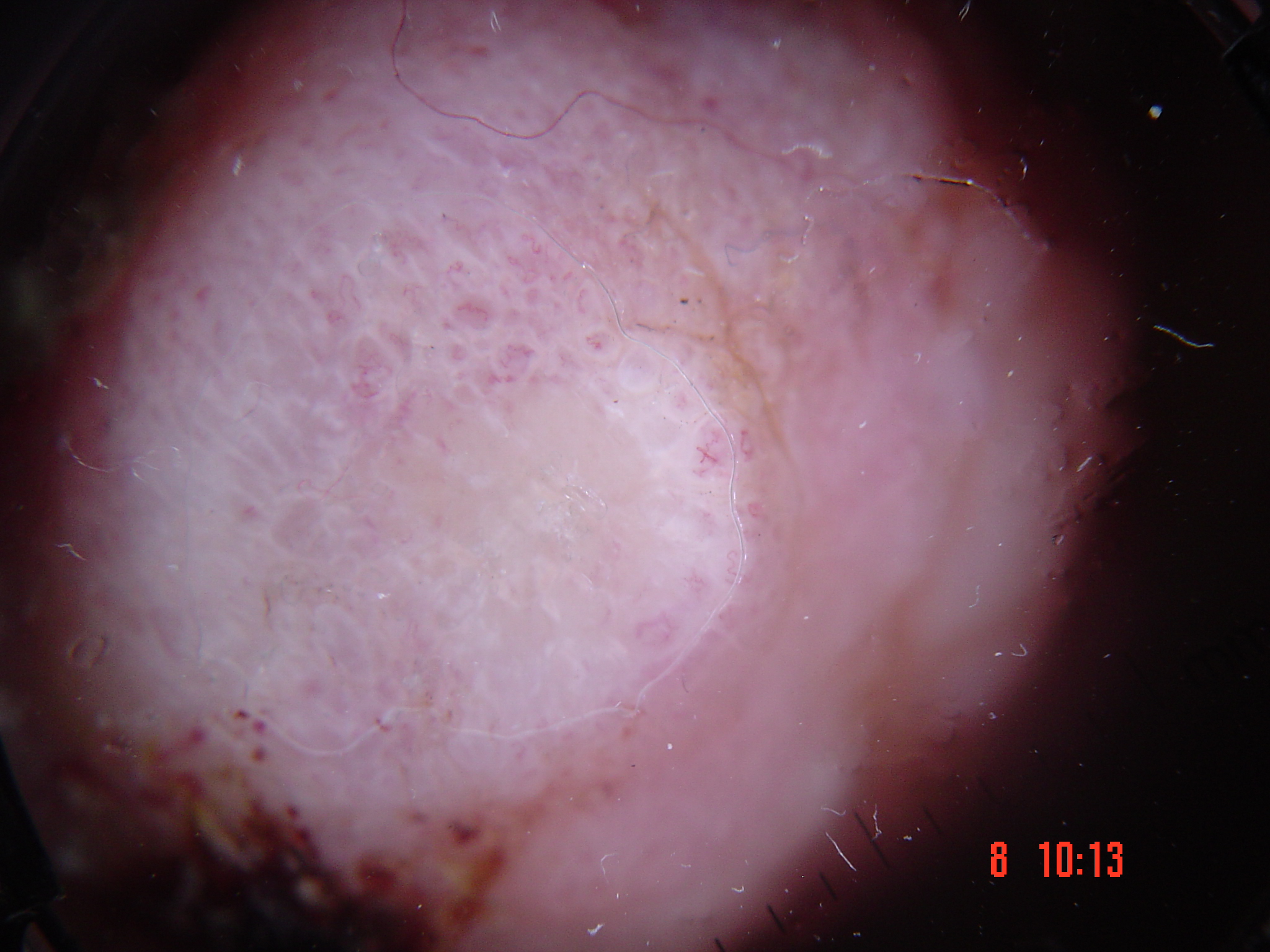A dermoscopic image of a skin lesion.
The biopsy diagnosis was a malignant lesion — an acral nodular melanoma.